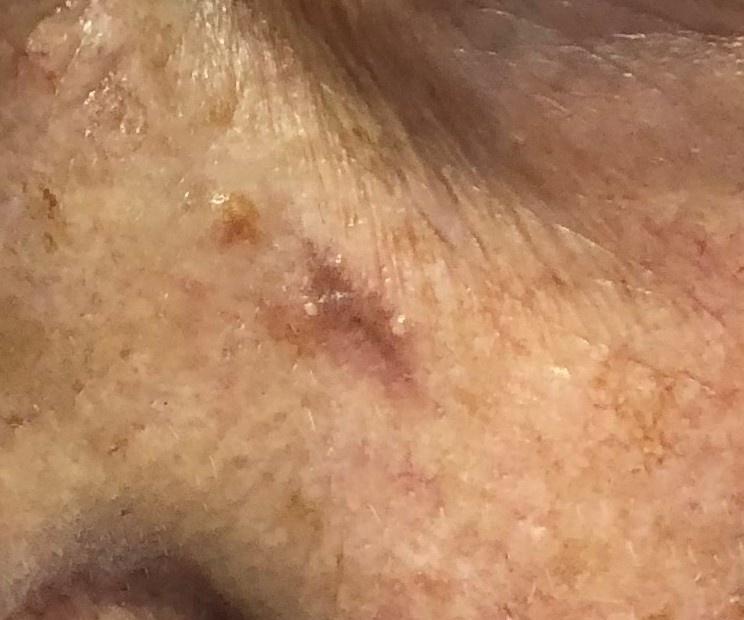Findings:
An overview clinical photograph of a skin lesion. A female patient aged approximately 80. The lesion is located on the head or neck.
Conclusion:
On biopsy, the diagnosis was a malignant lesion — a basal cell carcinoma.